A female subject approximately 75 years of age, dermoscopy of a skin lesion: 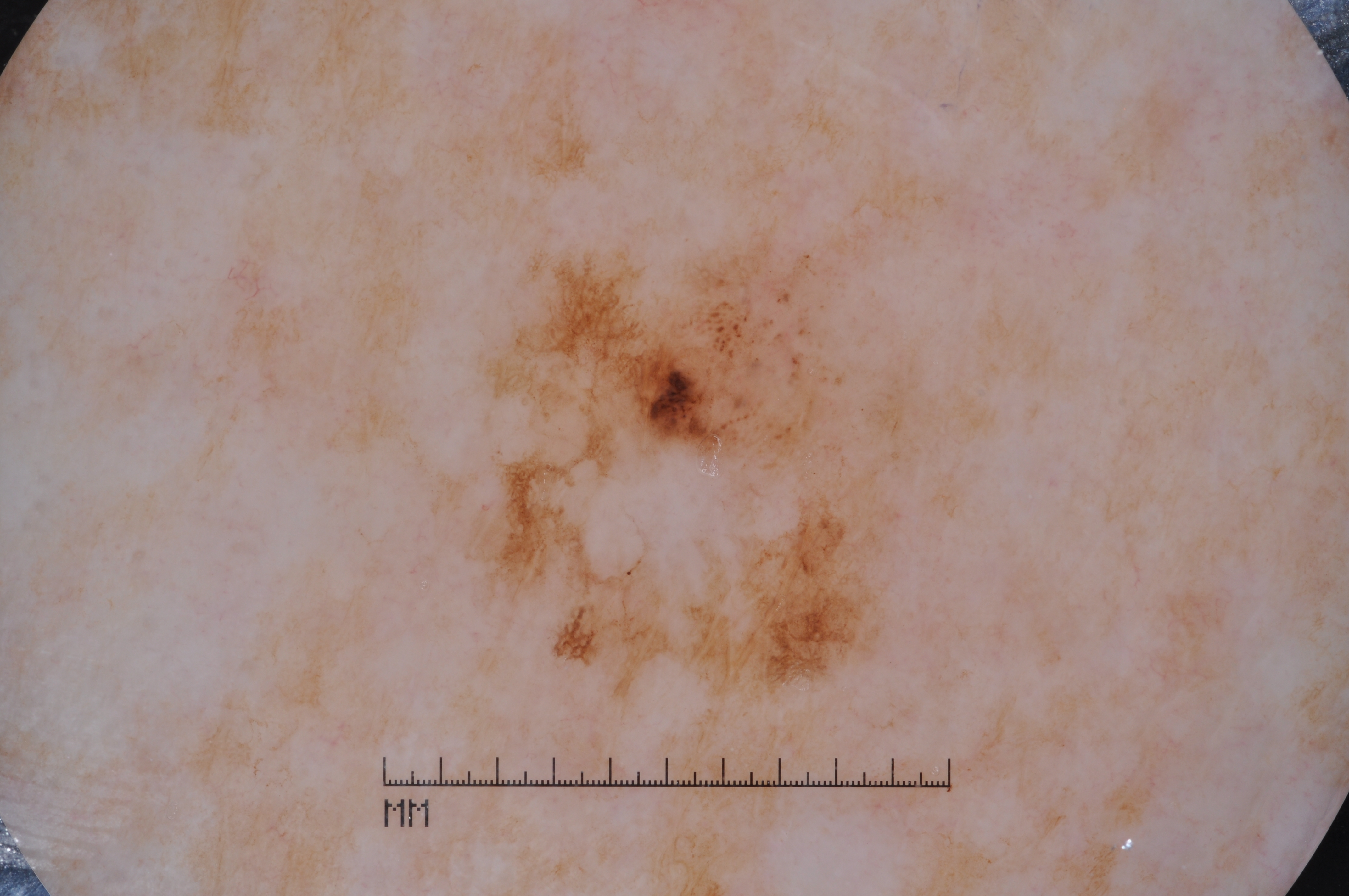Q: Lesion extent?
A: moderate
Q: What does dermoscopy show?
A: pigment network; absent: streaks, negative network, and milia-like cysts
Q: Where is the lesion located?
A: (471, 199, 916, 762)
Q: What is this lesion?
A: a melanoma, a skin cancer